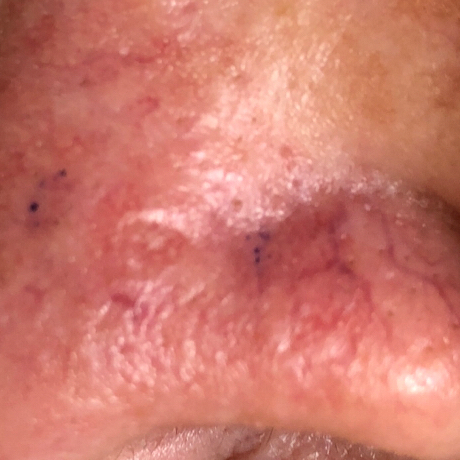Patient and lesion: A clinical photograph of a skin lesion. A female patient in their 50s. The chart records pesticide exposure, alcohol use, prior malignancy (patient or family), no prior skin cancer (patient or family), and no tobacco use. Measuring about 5 × 5 mm. The patient reports that the lesion is elevated. Diagnosis: Histopathology confirmed a basal cell carcinoma.